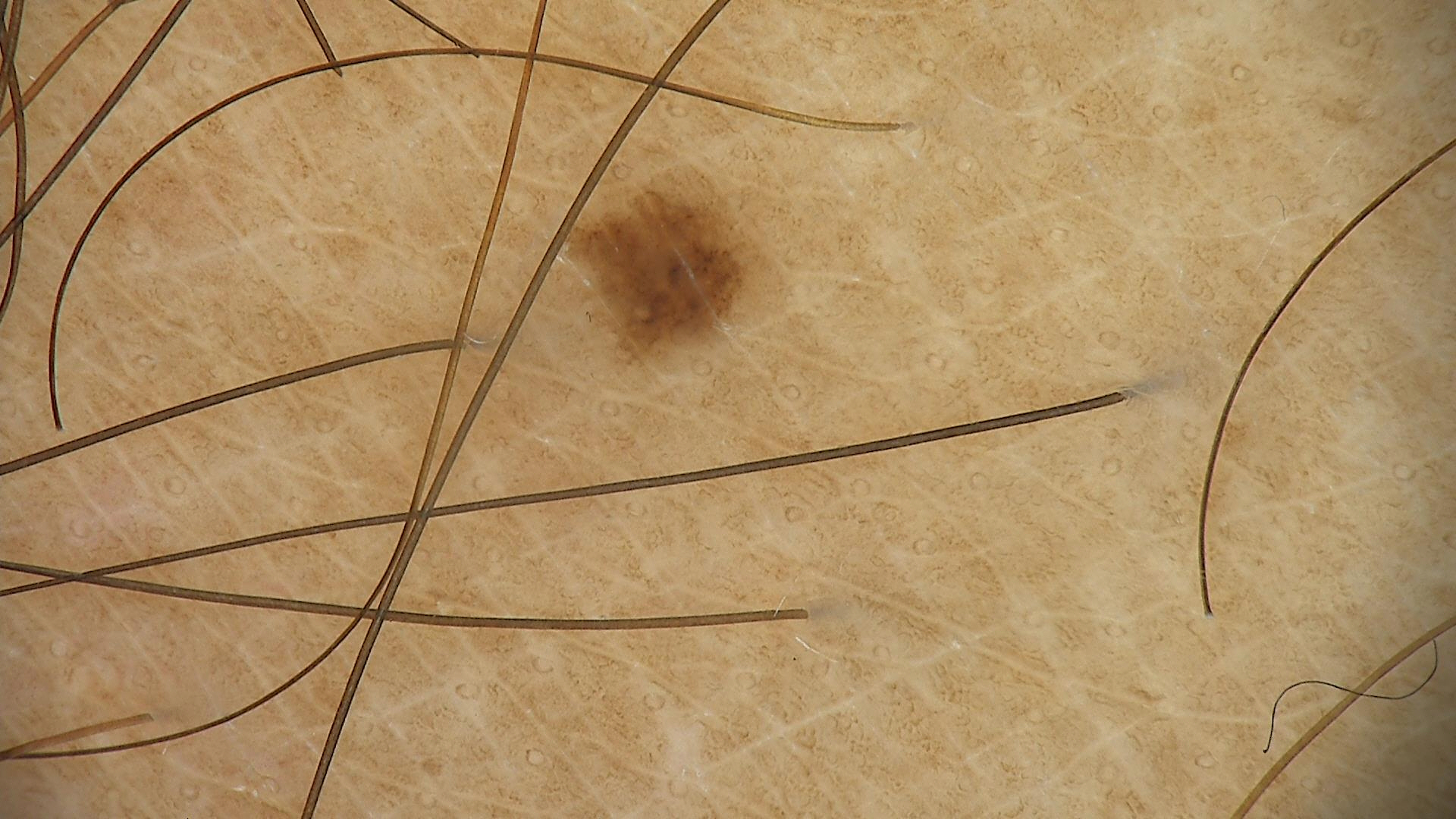A dermatoscopic image of a skin lesion. Labeled as a dysplastic junctional nevus.